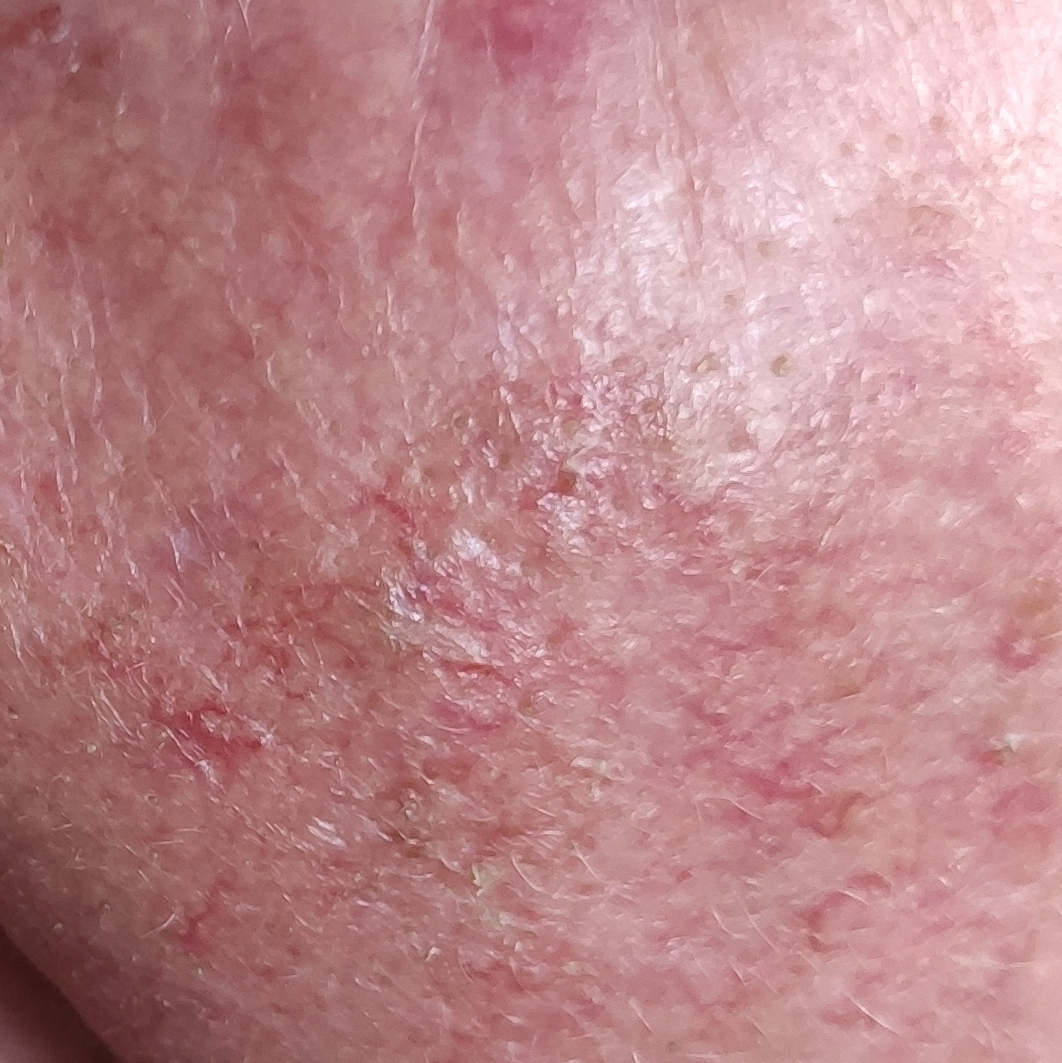A female patient aged 71.
The chart records pesticide exposure and prior skin cancer (patient or family).
The patient was assessed as Fitzpatrick phototype III.
A clinical photograph showing a skin lesion.
The lesion involves the face.
The lesion measures approximately 9 × 6 mm.
The patient reports that the lesion hurts, has grown, itches, is elevated, and has changed.
Histopathological examination showed a basal cell carcinoma.